A dermoscopic view of a skin lesion — 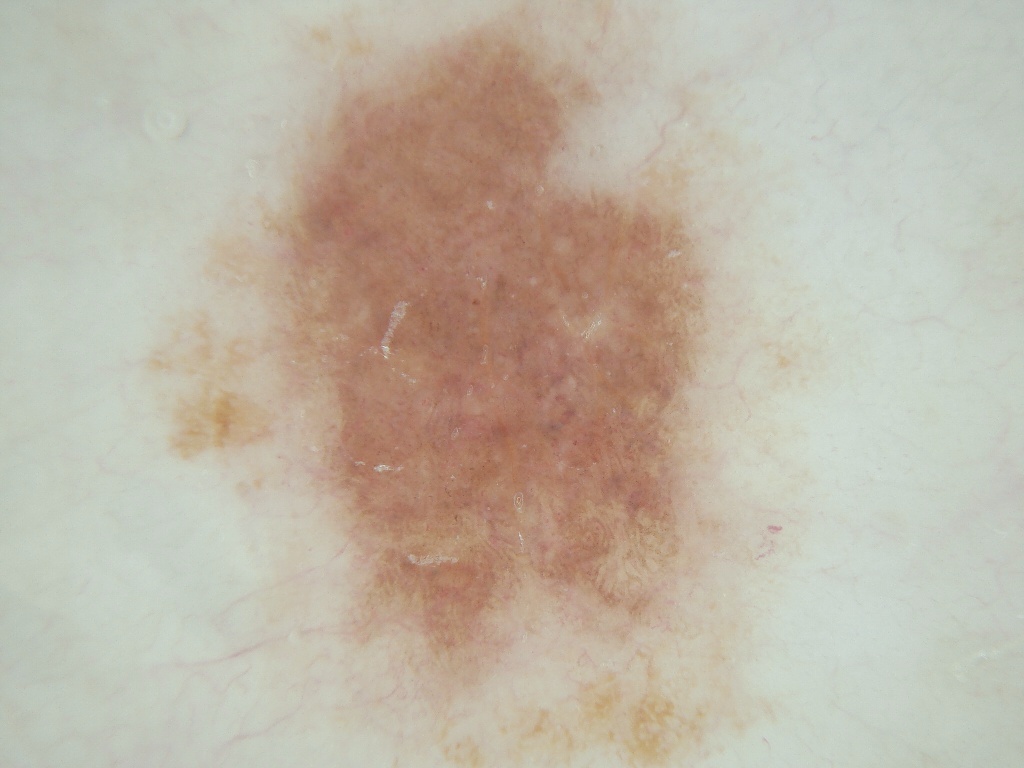bounding box — 144 3 833 766
impression — a benign lesion